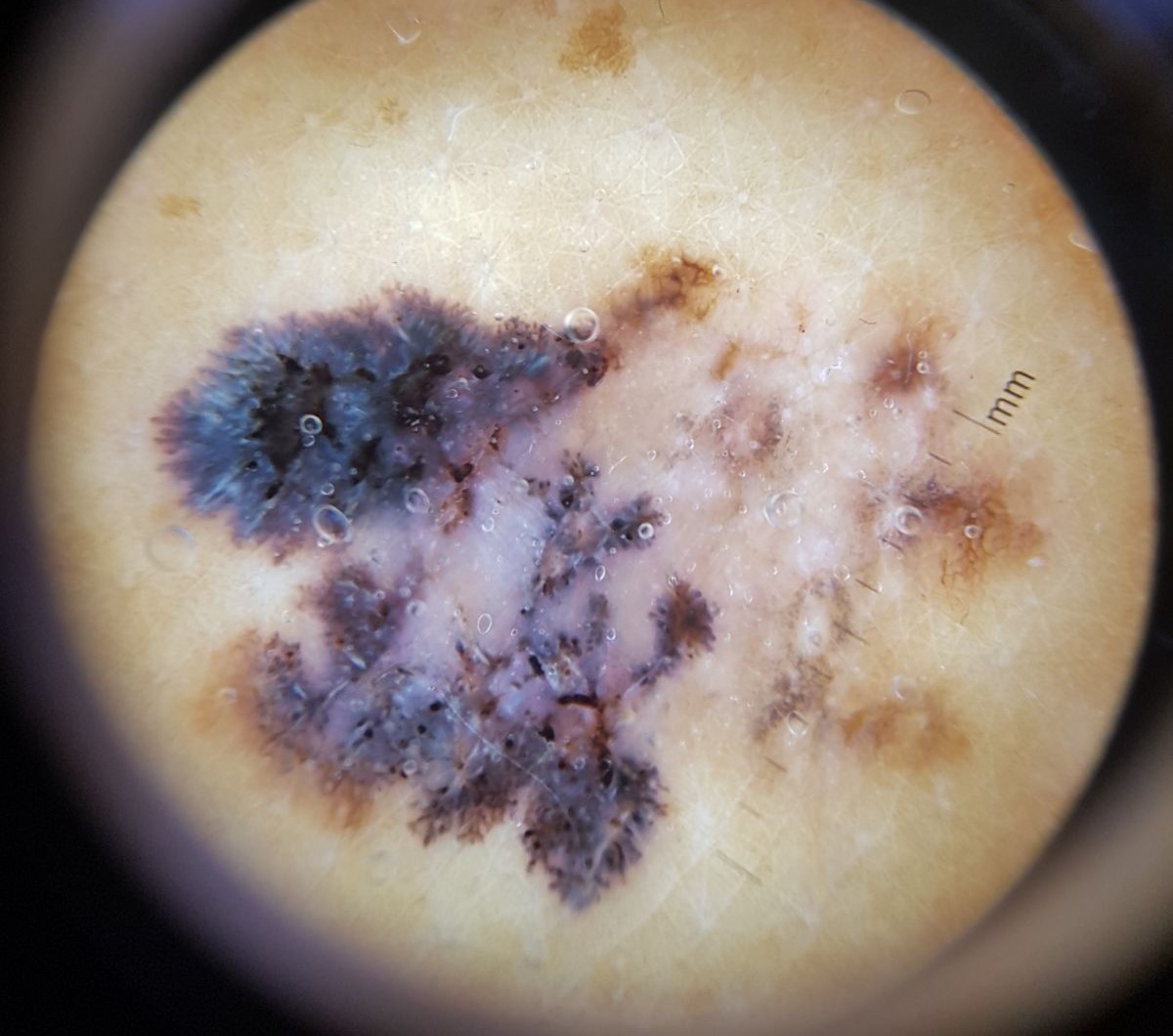Case:
- class — melanoma (biopsy-proven)